This image was taken at a distance; the affected area is the leg — 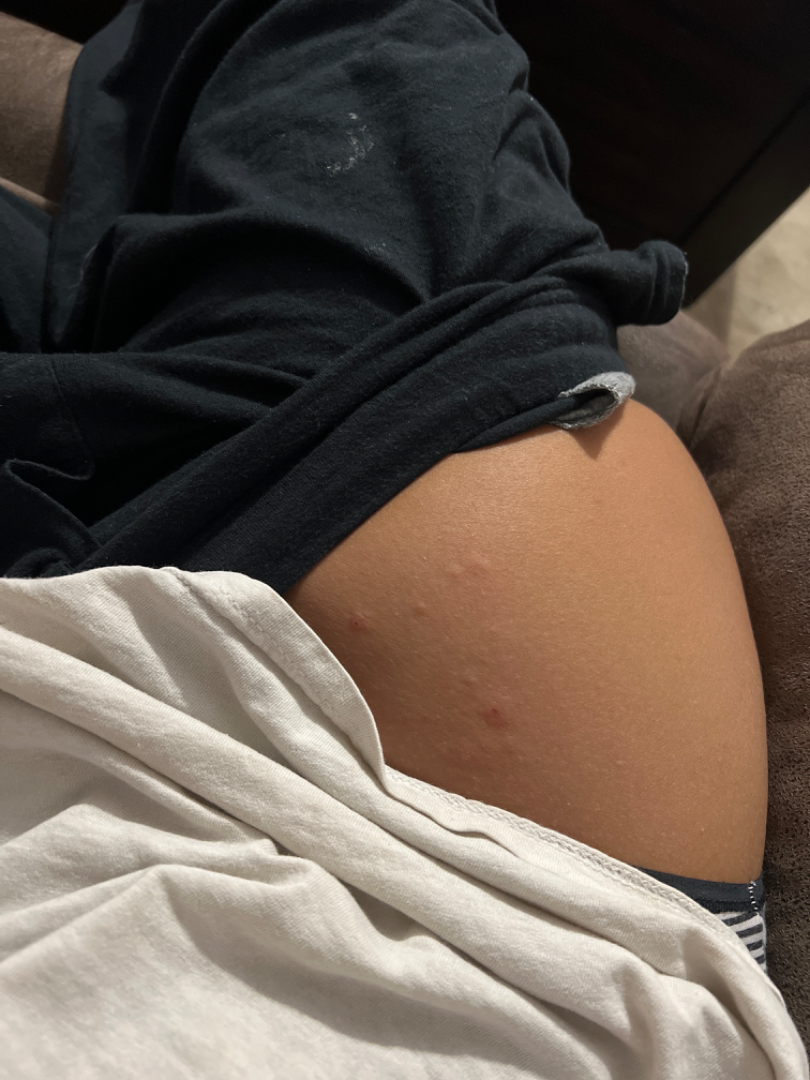The condition has been present for less than one week. Reported lesion symptoms include itching. Fitzpatrick phototype IV; human graders estimated 4 on the Monk skin tone scale. The contributor notes the lesion is raised or bumpy. On remote dermatologist review: Impetigo (weight 0.33); Insect Bite (weight 0.33); Herpes Simplex (weight 0.33).